The photograph was taken at an angle: 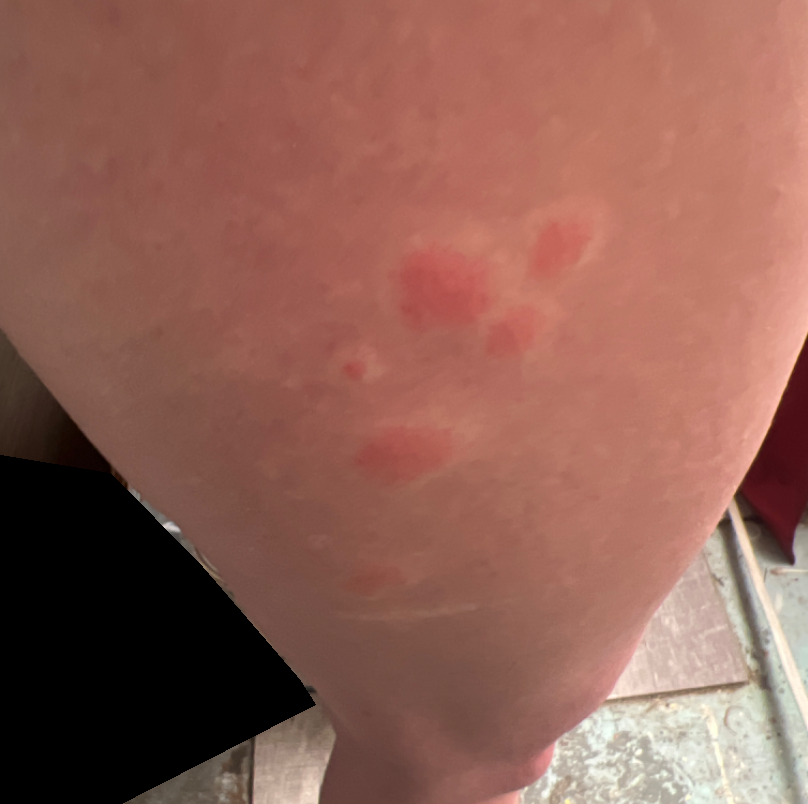Review:
The differential is split between Insect Bite and Eczema.